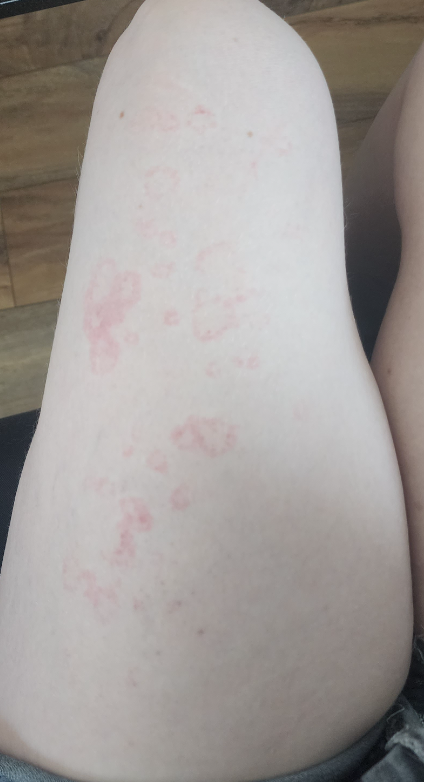history — one to four weeks | skin tone — non-clinician graders estimated MST 1 | framing — close-up | patient describes the issue as — a rash | patient — female, age 18–29 | symptoms — enlargement, itching and bothersome appearance | body site — leg | lesion texture — raised or bumpy | diagnostic considerations — favoring Urticaria.